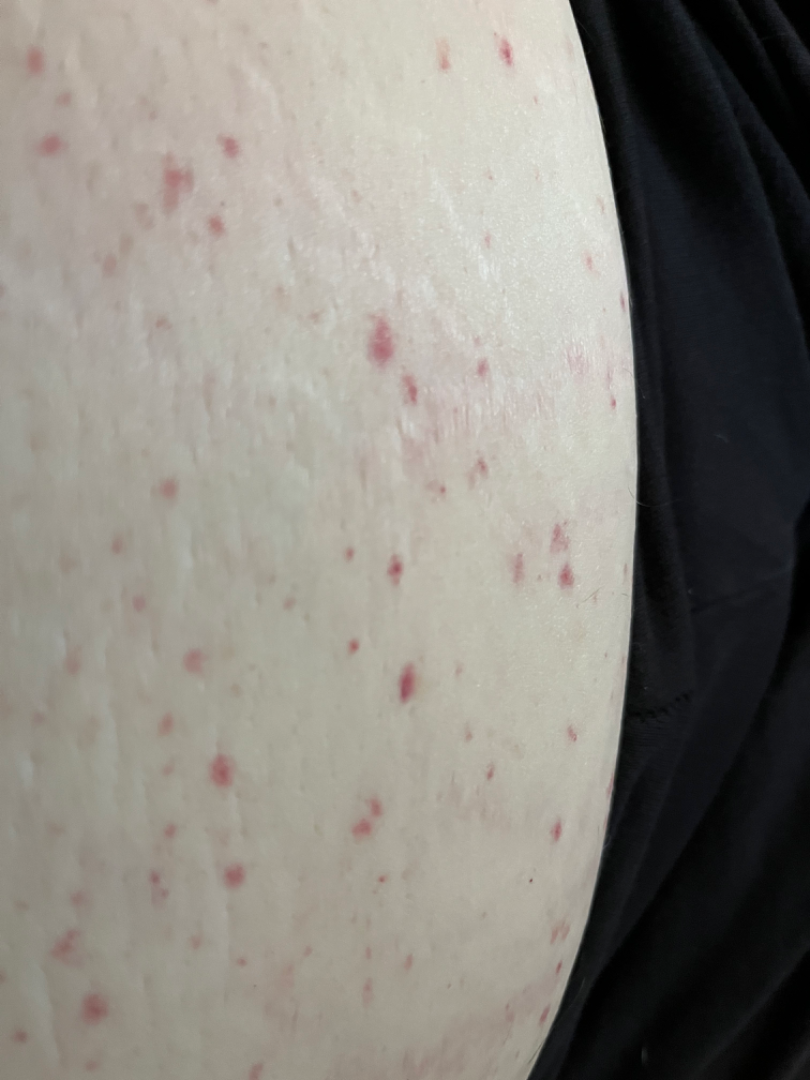The skin condition could not be confidently assessed from this image. The leg and front of the torso are involved. Female subject, age 50–59. Close-up view.